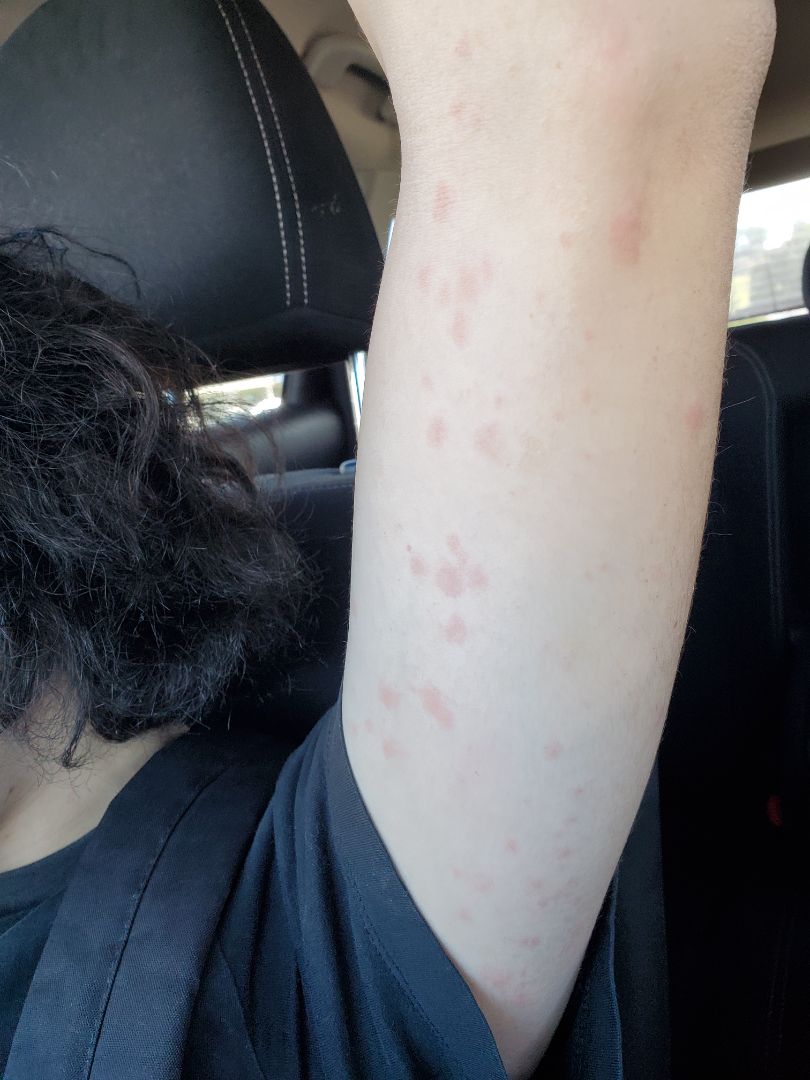Q: What was the assessment?
A: unable to determine
Q: Where on the body?
A: back of the hand, leg and arm
Q: Reported symptoms?
A: itching
Q: How long has this been present?
A: about one day
Q: How does the lesion feel?
A: flat
Q: Image view?
A: close-up